History notes prior skin cancer (patient or family). The patient was assessed as FST II. A female patient 14 years old. A smartphone photograph of a skin lesion.
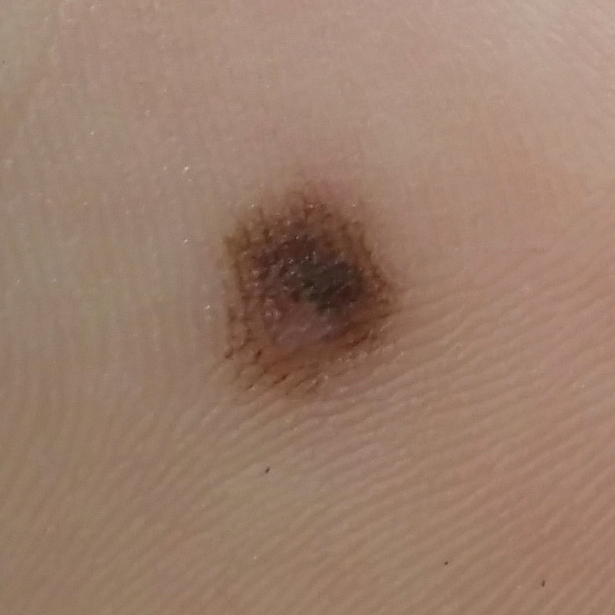<skin_lesion>
<lesion_location>a foot</lesion_location>
<lesion_size>
<diameter_1_mm>3.0</diameter_1_mm>
<diameter_2_mm>3.0</diameter_2_mm>
</lesion_size>
<symptoms>
<present>change in appearance, growth</present>
</symptoms>
<diagnosis>
<name>nevus</name>
<code>NEV</code>
<malignancy>benign</malignancy>
<confirmation>histopathology</confirmation>
</diagnosis>
</skin_lesion>